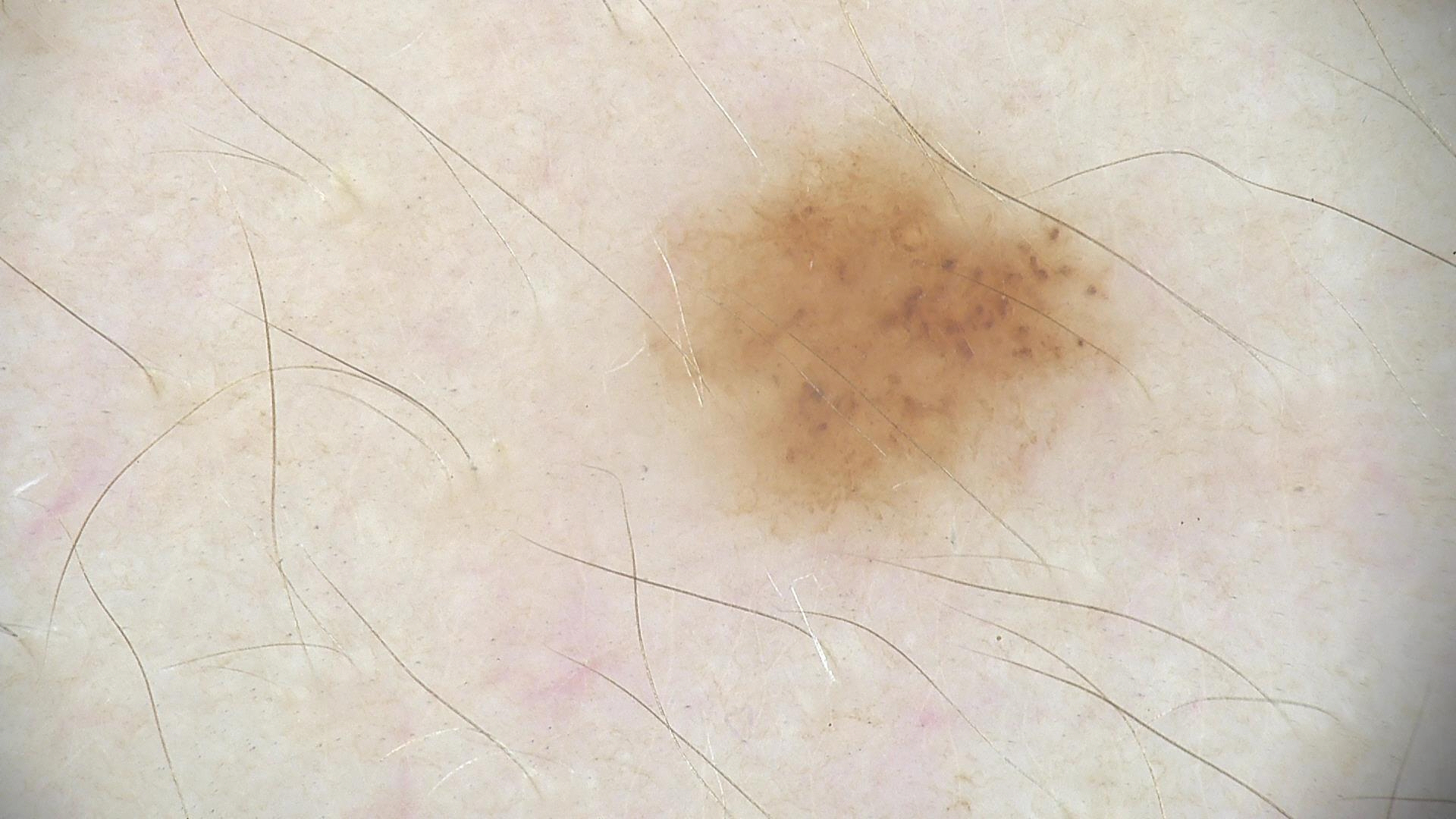The diagnosis was a benign lesion — a dysplastic junctional nevus.